The patient considered this a rash, the photo was captured at an angle — 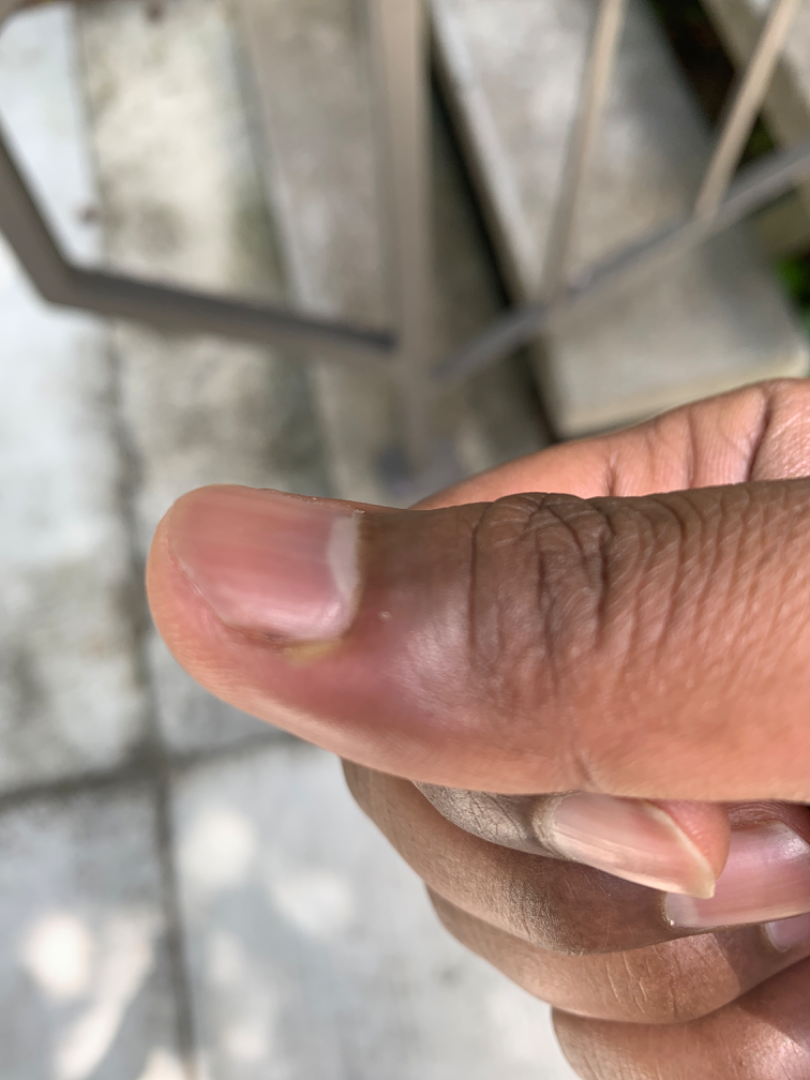Favoring Paronychia; the differential also includes Herpes Simplex; also raised was Eczema.